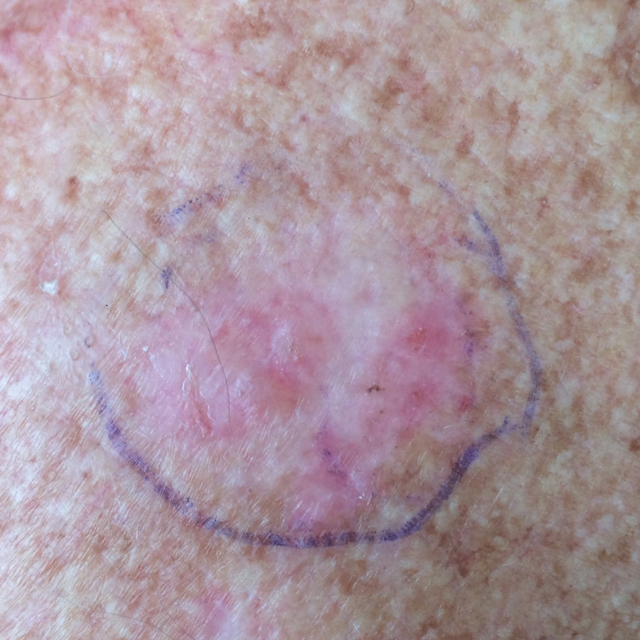  risk_factors:
    positive:
      - pesticide exposure
      - prior cancer (patient or family)
  image: clinical photograph
  skin_type: II
  lesion_size:
    diameter_1_mm: 3.0
    diameter_2_mm: 3.0
  symptoms:
    present:
      - itching
  diagnosis:
    name: squamous cell carcinoma
    code: SCC
    malignancy: malignant
    confirmation: histopathology